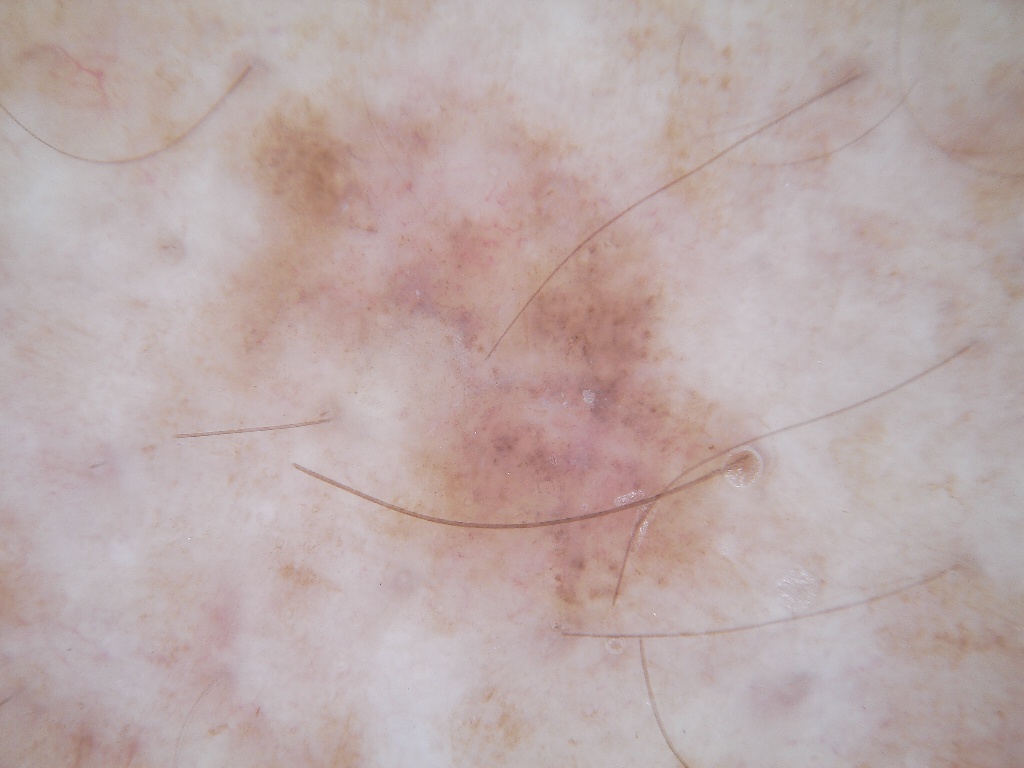| key | value |
|---|---|
| modality | dermoscopy |
| absent dermoscopic findings | pigment network, negative network, milia-like cysts, streaks, and globules |
| lesion location | bbox=[193, 77, 790, 663] |
| diagnosis | a melanoma |